Dermoscopy of a skin lesion.
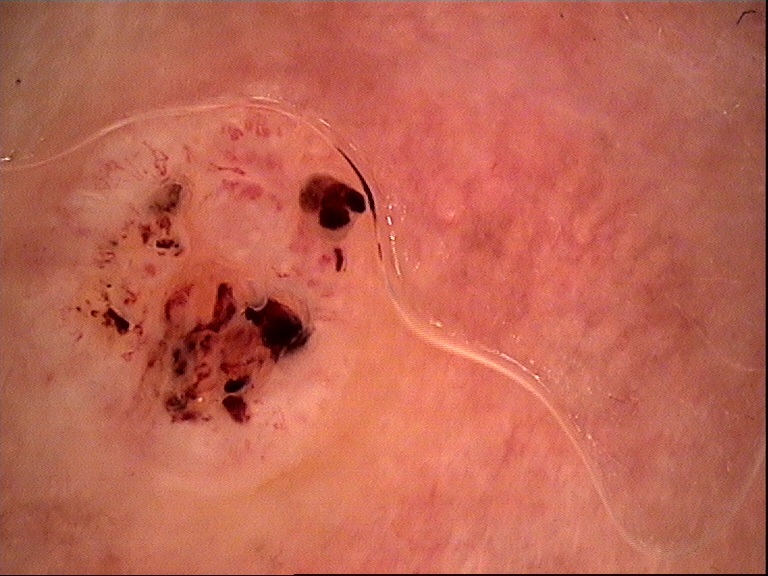pathology — basal cell carcinoma (biopsy-proven).